The lesion is described as raised or bumpy. Close-up view. Reported duration is less than one week. Female contributor, age 40–49. Self-categorized by the patient as a rash. Symptoms reported: itching. The lesion involves the back of the hand, arm and leg — 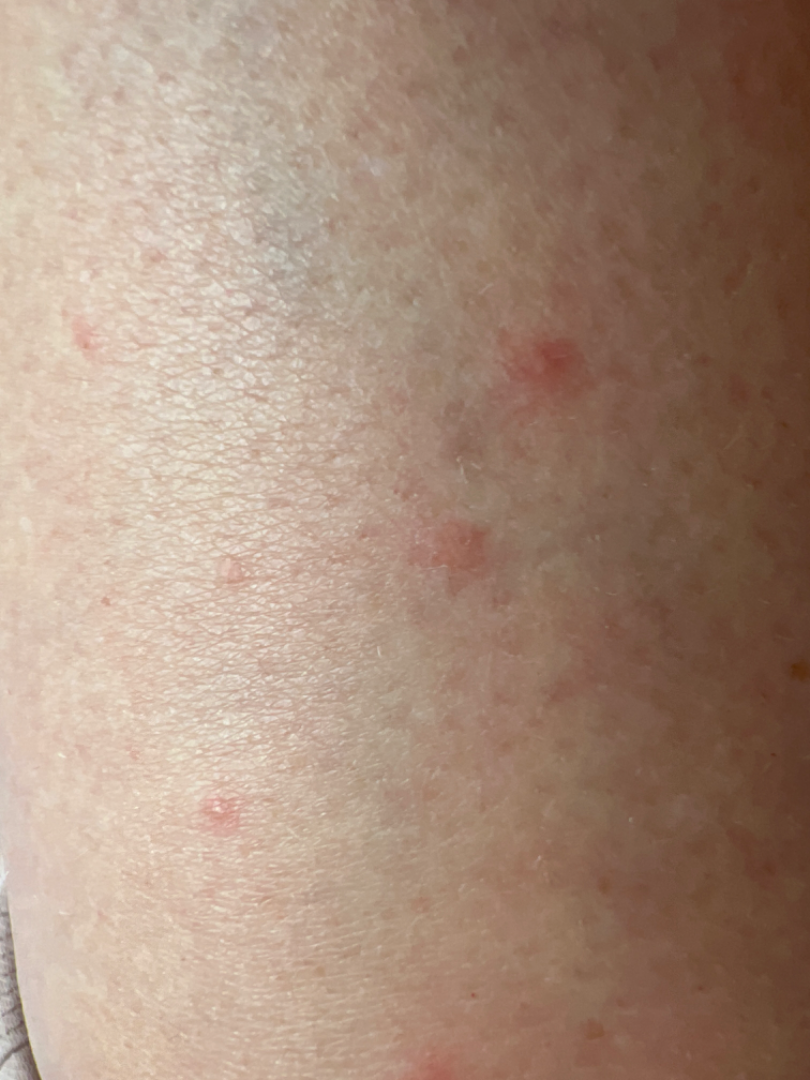Q: What is the dermatologist's impression?
A: consistent with Folliculitis